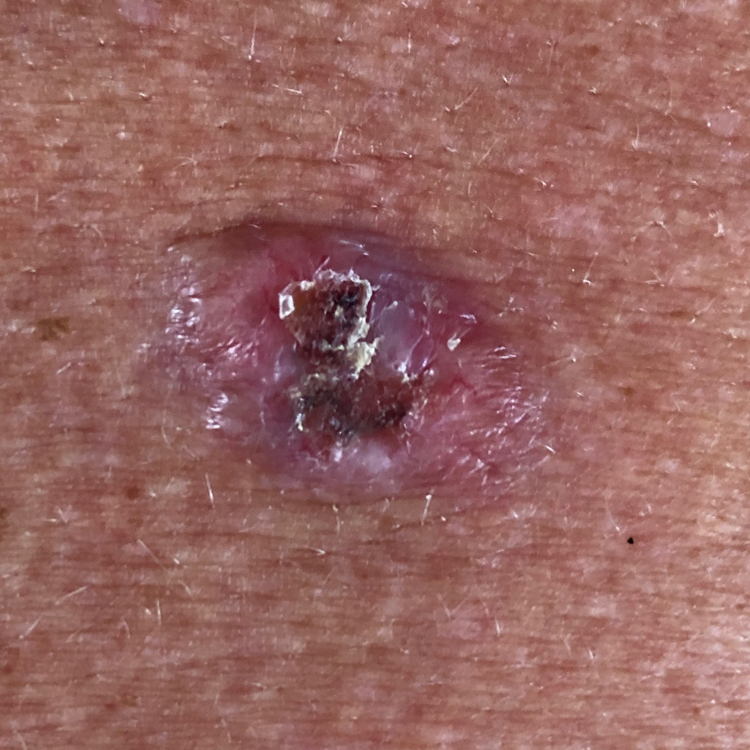subject: male, in their late 60s | modality: clinical photo | skin phototype: II | exposure history: pesticide exposure, prior skin cancer (patient or family), prior malignancy (patient or family) | pathology: basal cell carcinoma (biopsy-proven).